A dermoscopic image of a skin lesion.
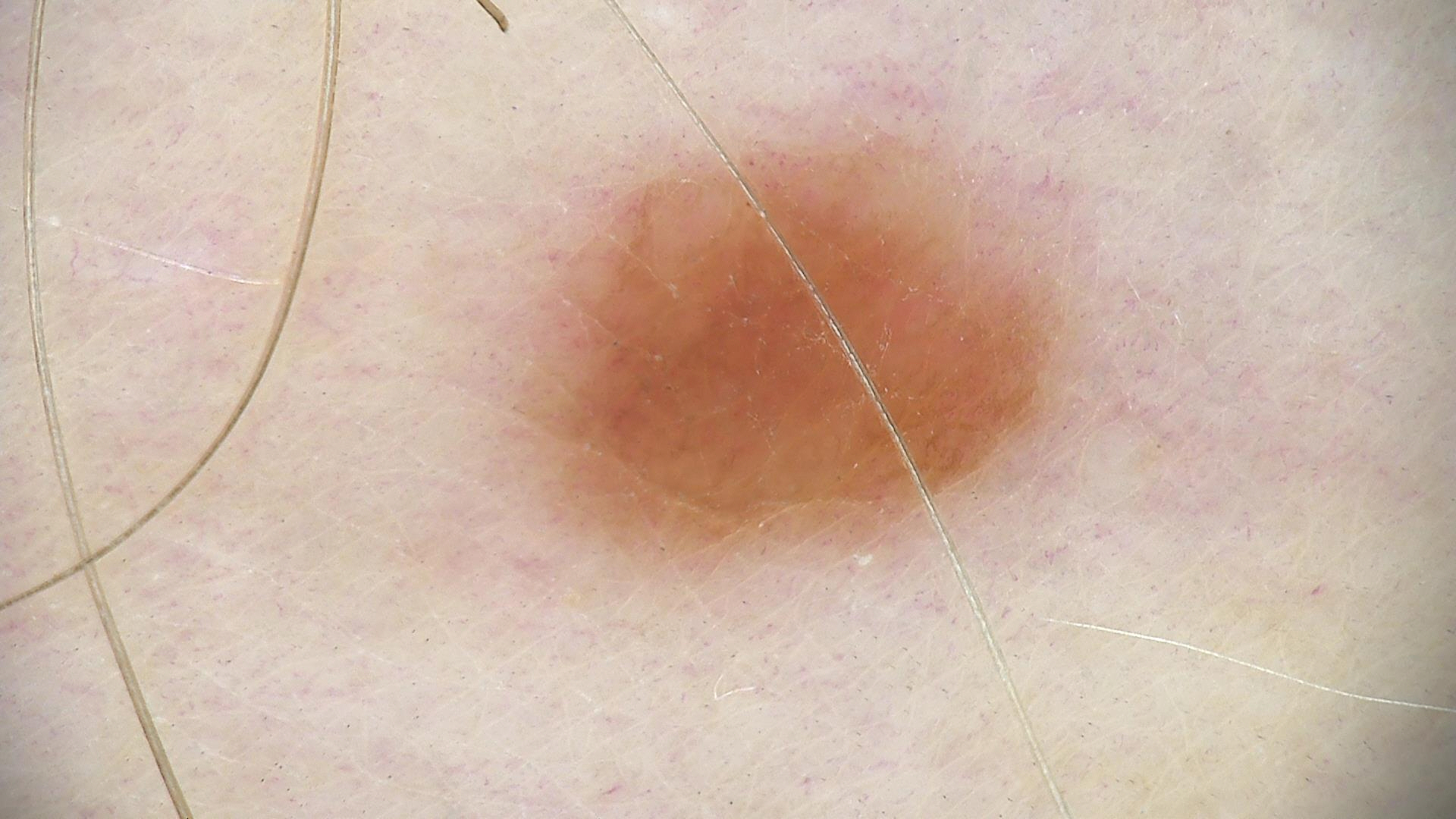Conclusion: Labeled as a banal lesion — a junctional nevus.